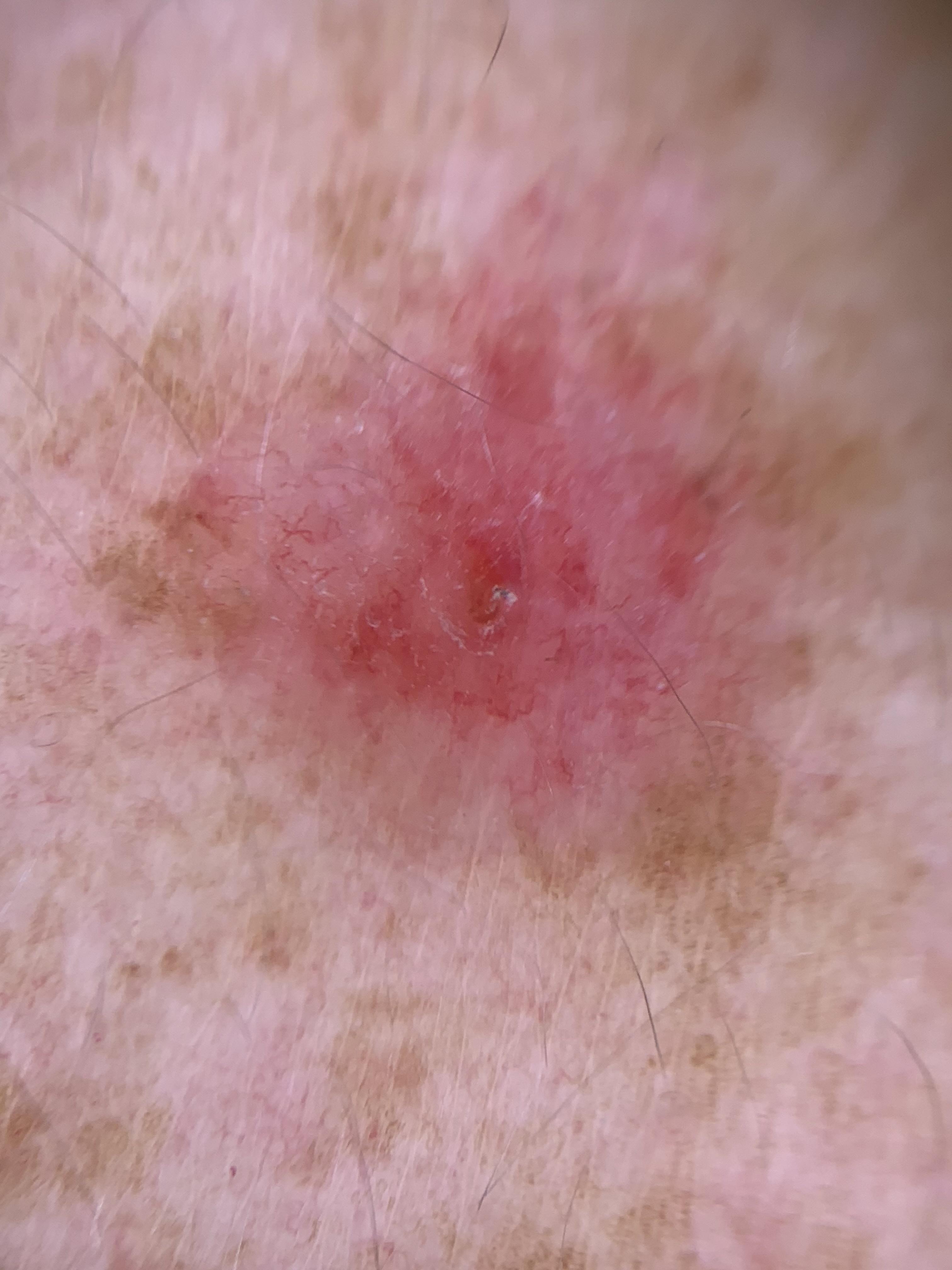Findings:
– subject: female, in their mid- to late 40s
– image type: dermoscopic image
– melanoma history: a first-degree relative with melanoma
– skin type: II
– location: the trunk
– diagnostic label: Basal cell carcinoma (biopsy-proven)